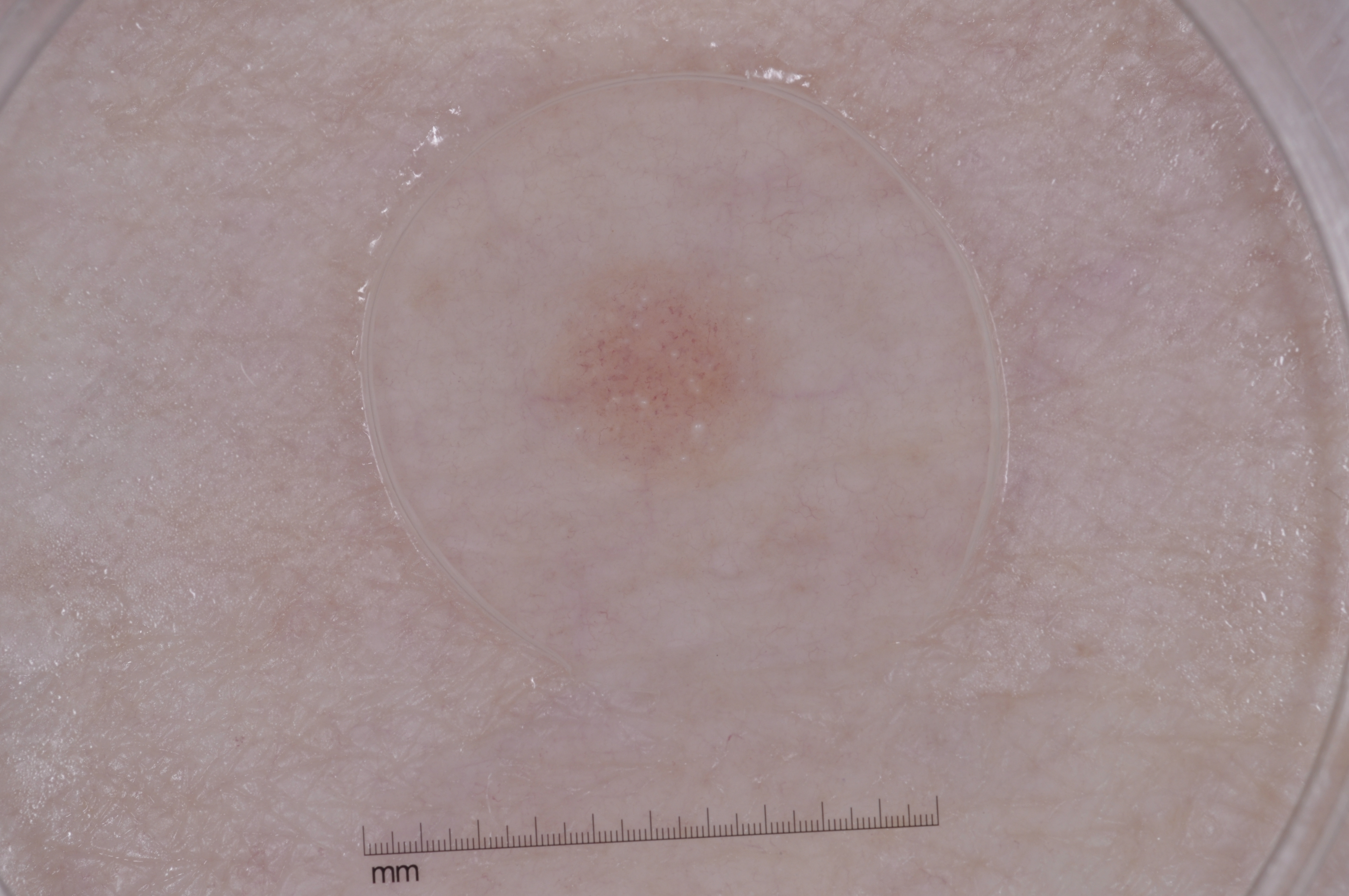imaging = dermoscopic image | dermoscopic pattern = milia-like cysts; absent: pigment network, streaks, and negative network | bounding box = <bbox>485, 252, 790, 518</bbox> | diagnosis = a melanocytic nevus, a benign lesion.